The contributor is female, the lesion involves the arm, the photo was captured at an angle:
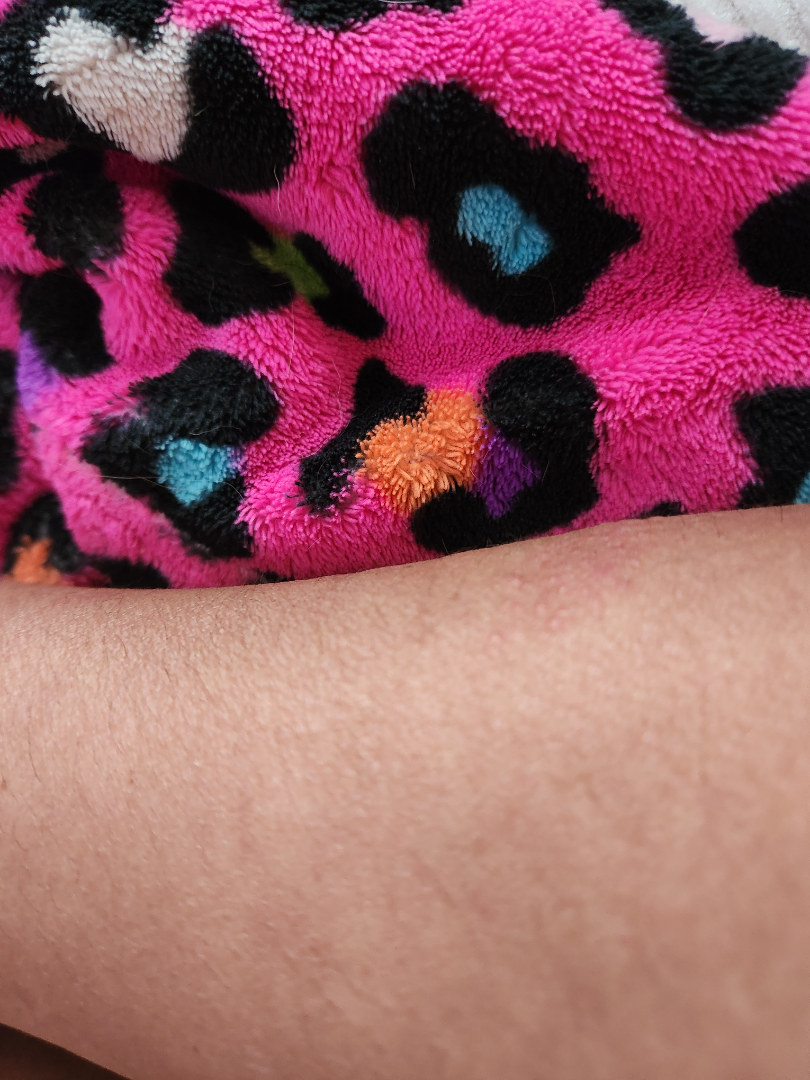impression — Eczema (weight 0.50); Contact dermatitis (weight 0.29); Psoriasis (weight 0.21).